Texture is reported as raised or bumpy and rough or flaky · reported duration is one to four weeks · the contributor is a male aged 18–29 · the contributor reports itching · the photograph was taken at a distance · the affected area is the back of the hand:
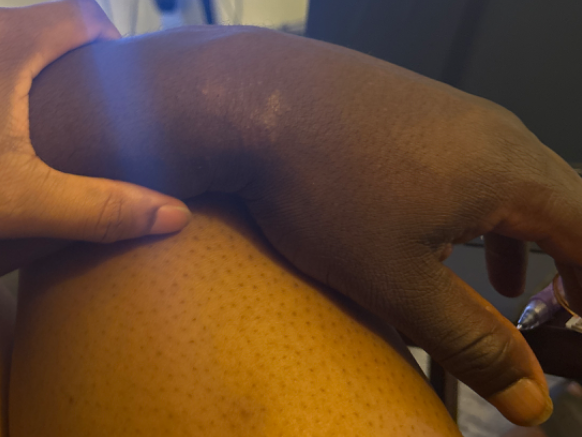Three independent reviewers: the favored diagnosis is Eczema; less probable is Psoriasis; less likely is Lichen planus/lichenoid eruption.